The photograph is a close-up of the affected area.
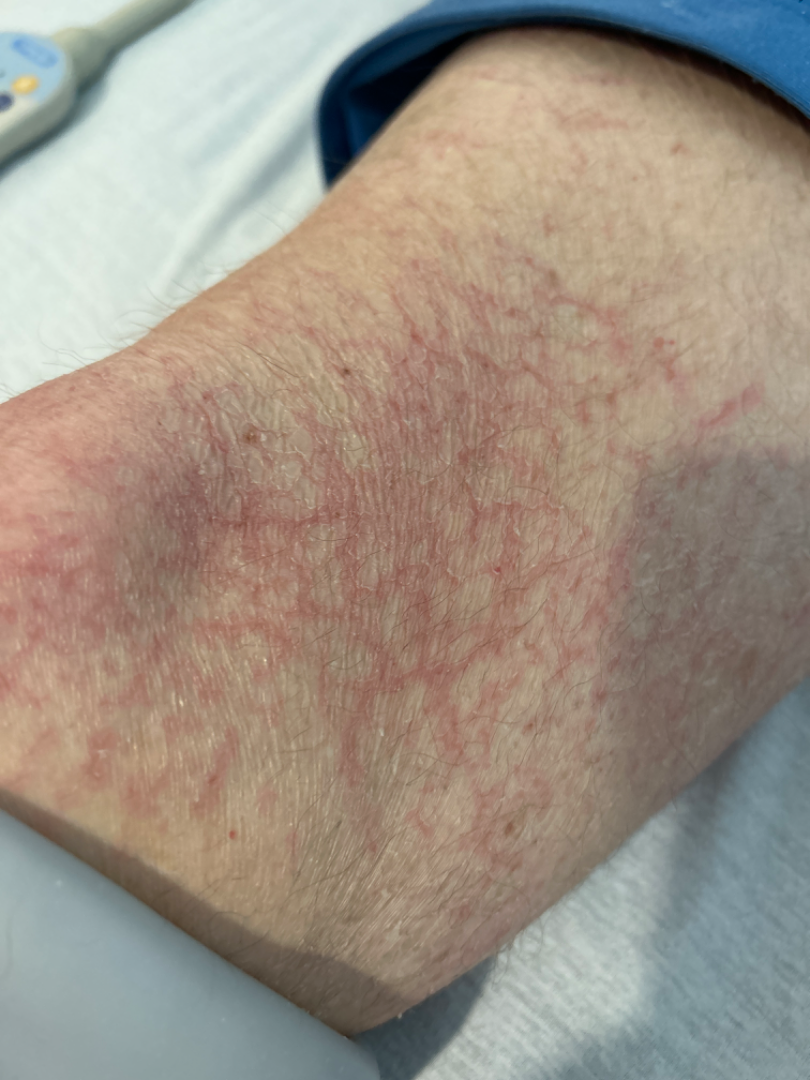Impression:
On remote review of the image: Eczema (favored).